The patient is Fitzpatrick II. The chart notes prior malignancy (patient or family), tobacco use, and prior skin cancer (patient or family). A clinical close-up photograph of a skin lesion: 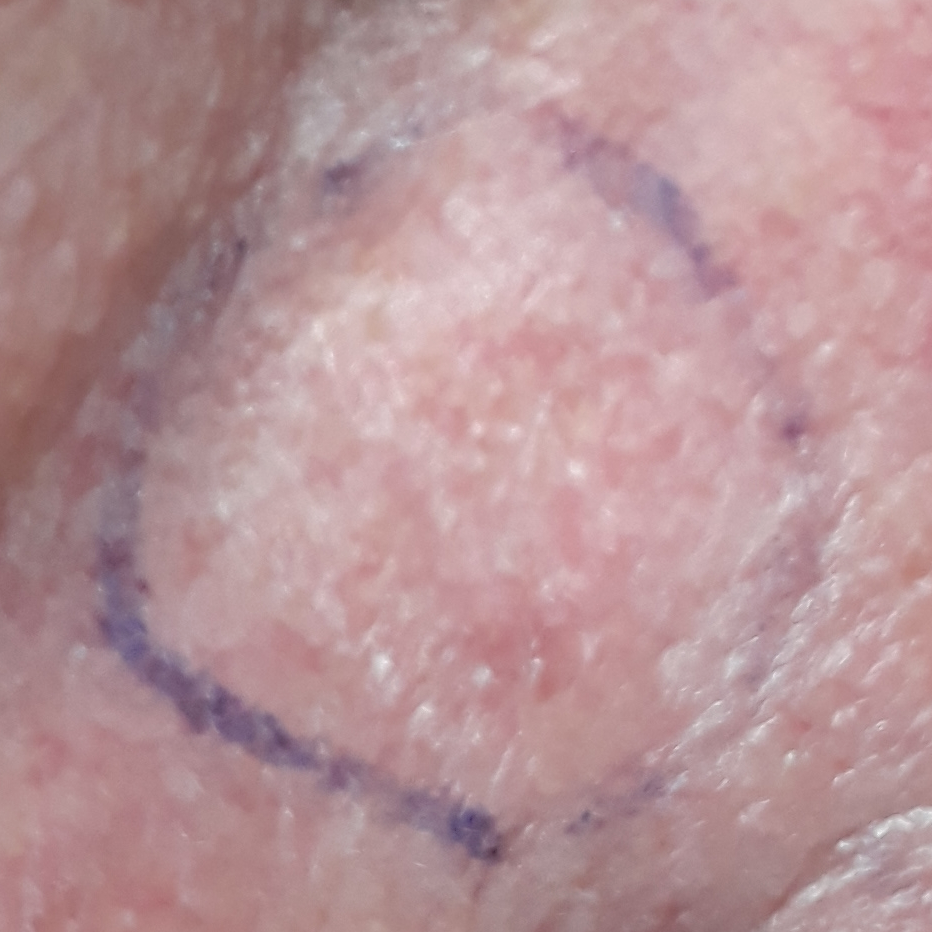The lesion measures 10 × 10 mm. The patient reports that the lesion has not grown and is not elevated. On biopsy, the diagnosis was an actinic keratosis.